A dermatoscopic image of a skin lesion.
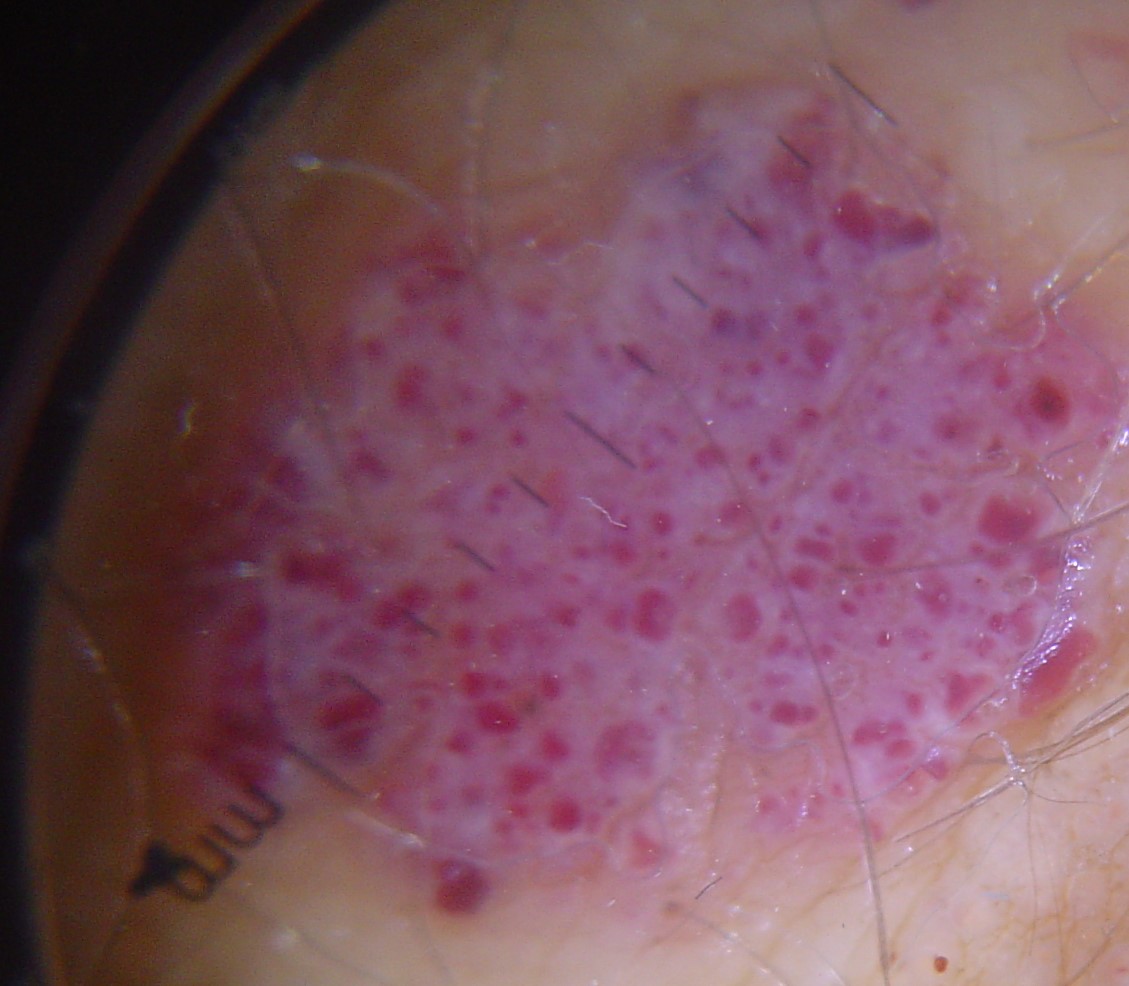Q: What kind of lesion is this?
A: vascular
Q: What is the diagnosis?
A: hemangioma (expert consensus)